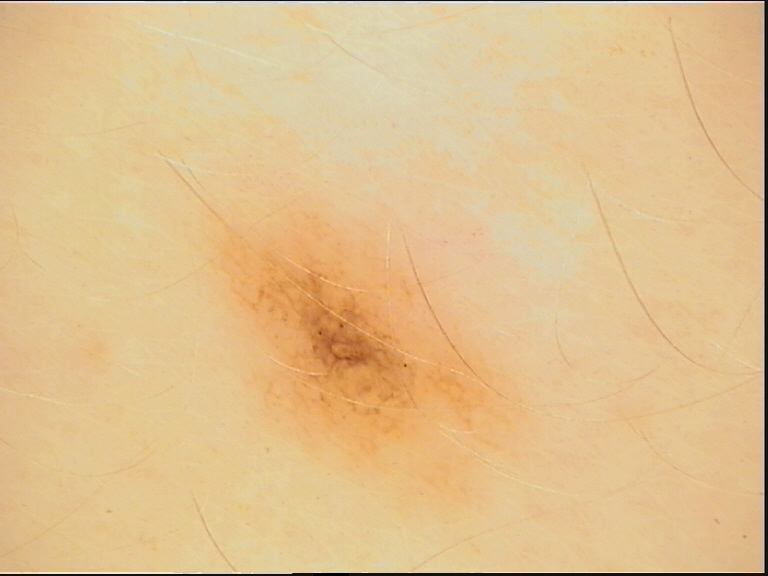Labeled as a dysplastic junctional nevus.